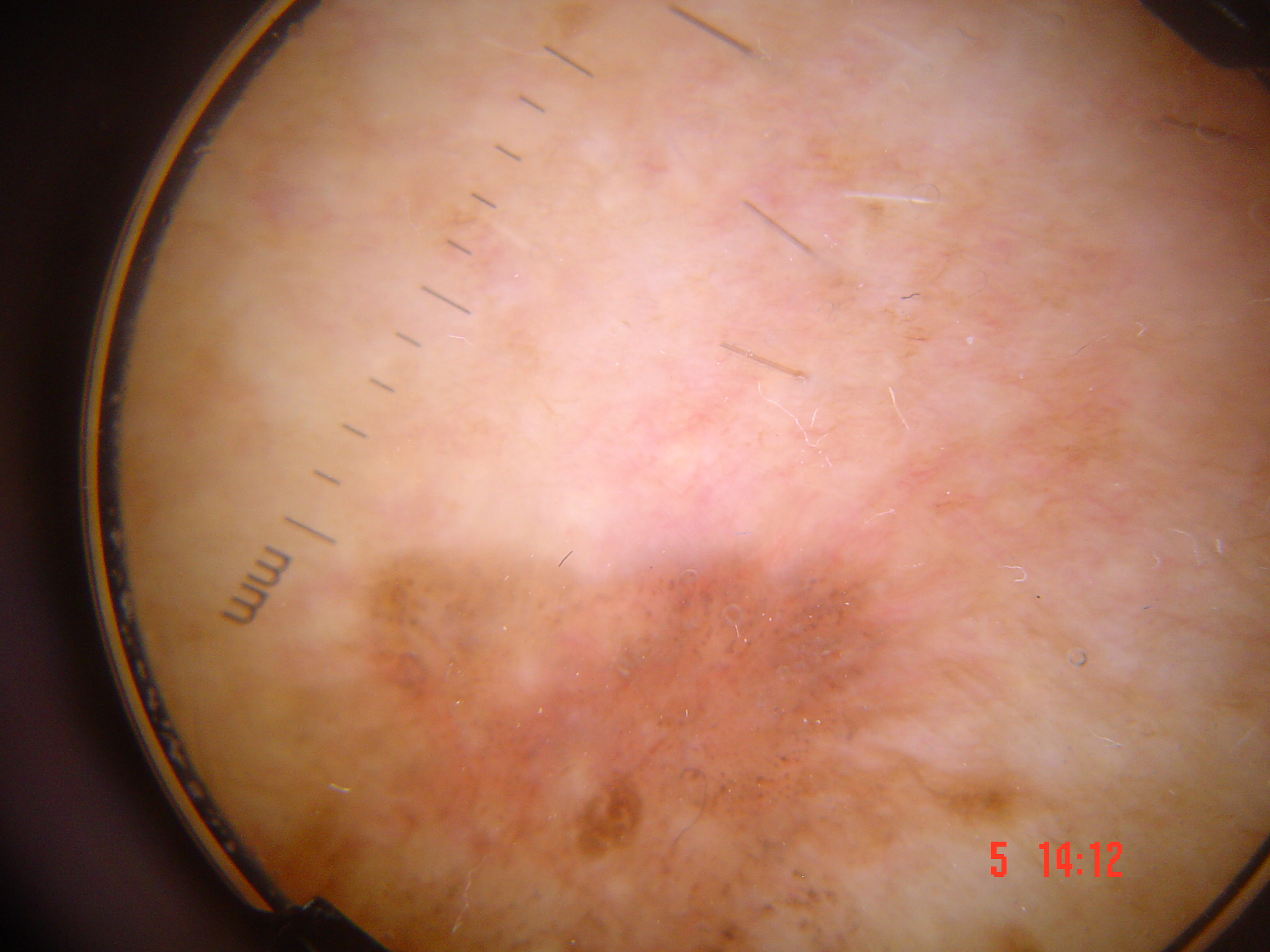Confirmed on histopathology as Bowen's disease.